A dermoscopy image of a single skin lesion; a female subject, aged 13-17 — 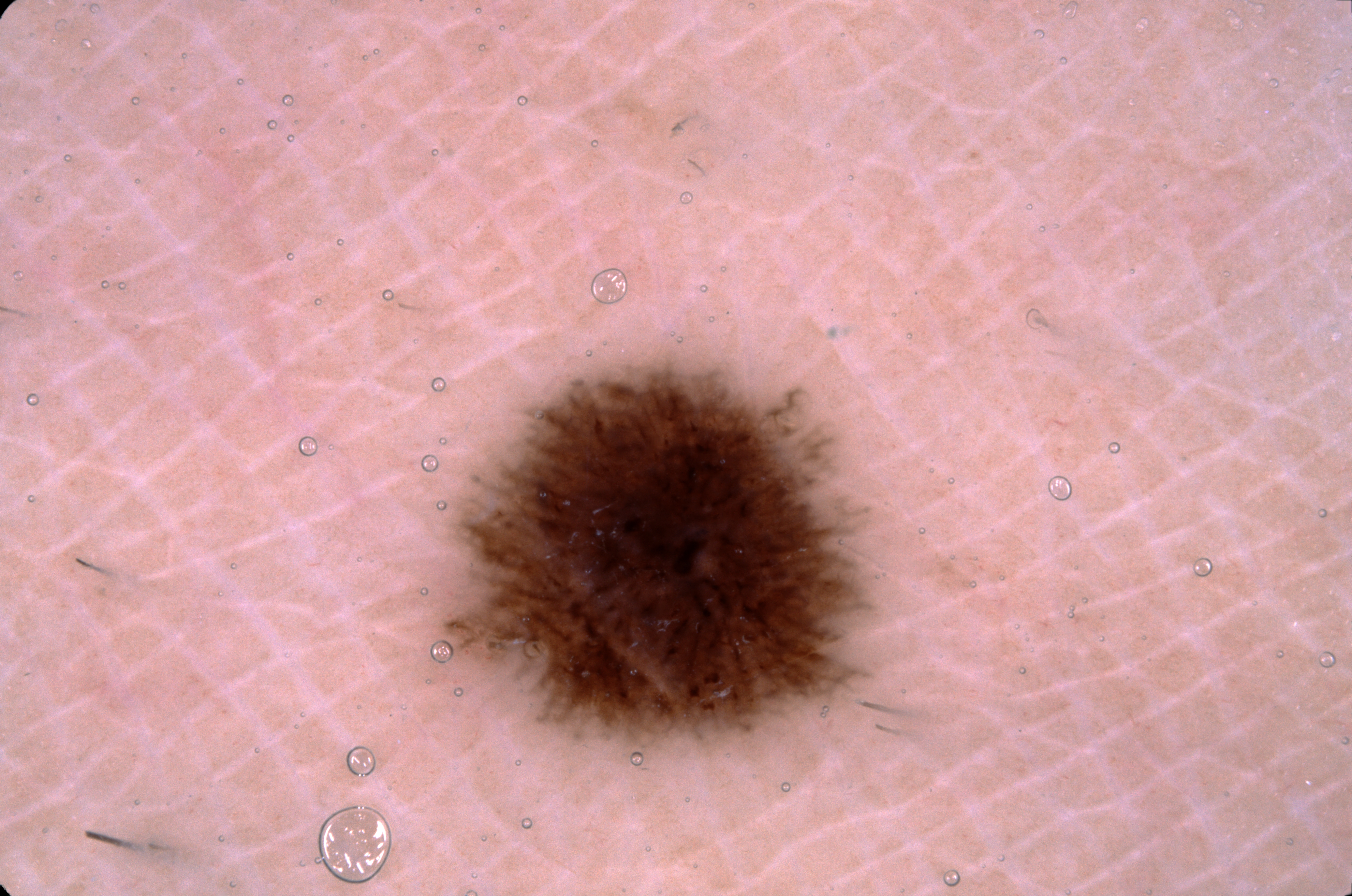Findings: Dermoscopy demonstrates pigment network, with no negative network, streaks, or milia-like cysts. The lesion occupies the region left=435, top=351, right=879, bottom=766. Impression: Clinically diagnosed as a melanocytic nevus, a benign skin lesion.